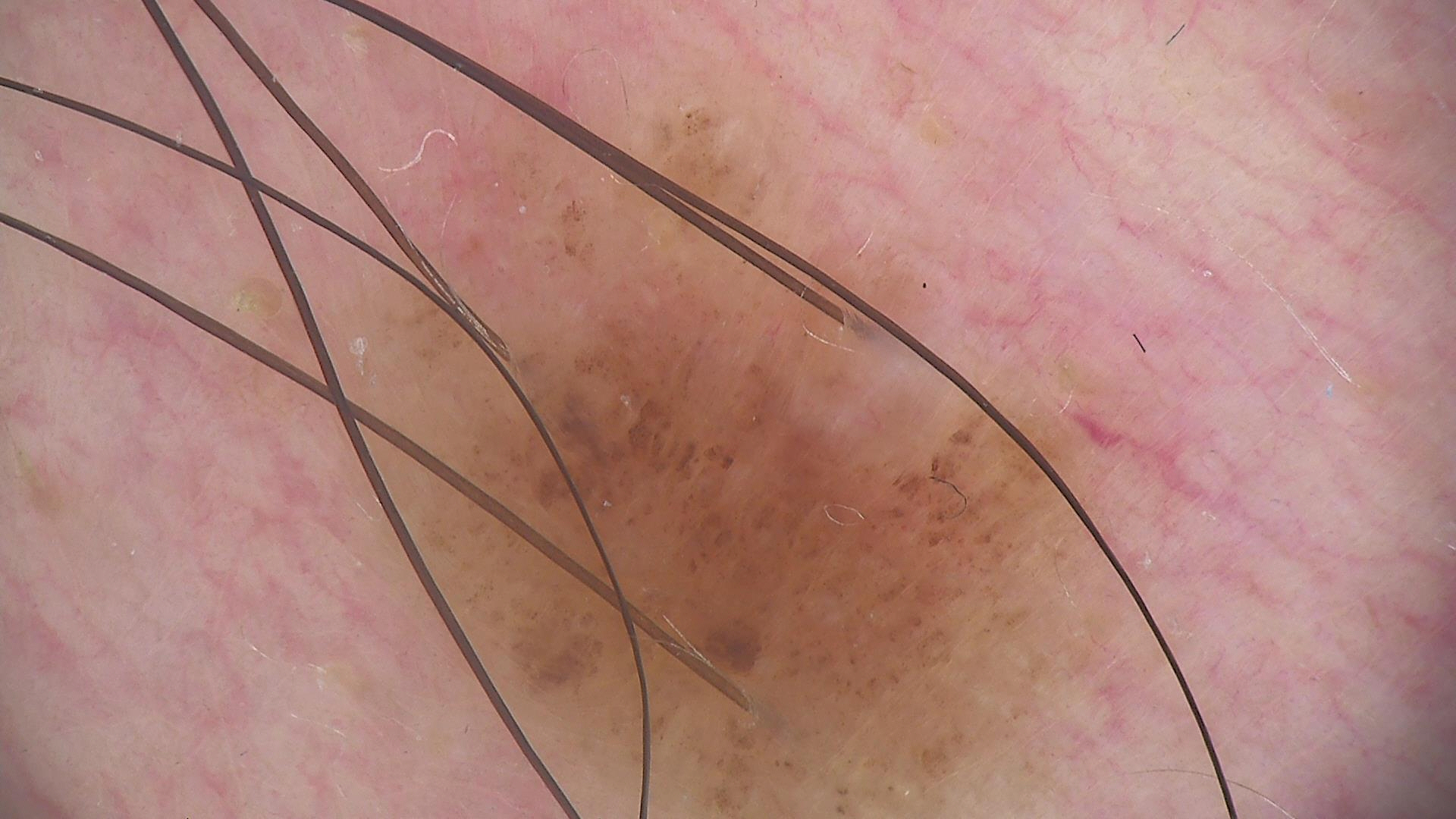Findings: A dermoscopic photograph of a skin lesion. The morphology is that of a banal lesion. Impression: The diagnosis was a compound nevus.